A male subject roughly 70 years of age:
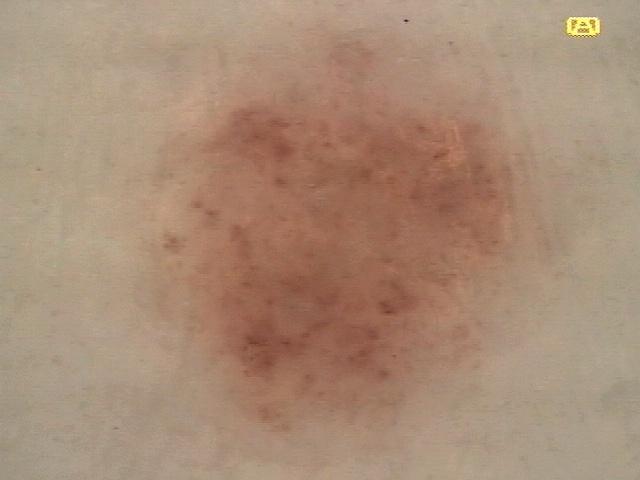The lesion involves the head or neck. The diagnostic impression was a solar or actinic keratosis.